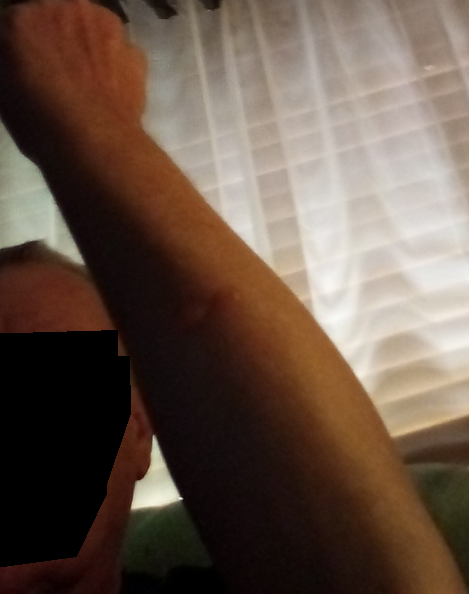| field | value |
|---|---|
| impression | in keeping with Bullous Pemphigoid |